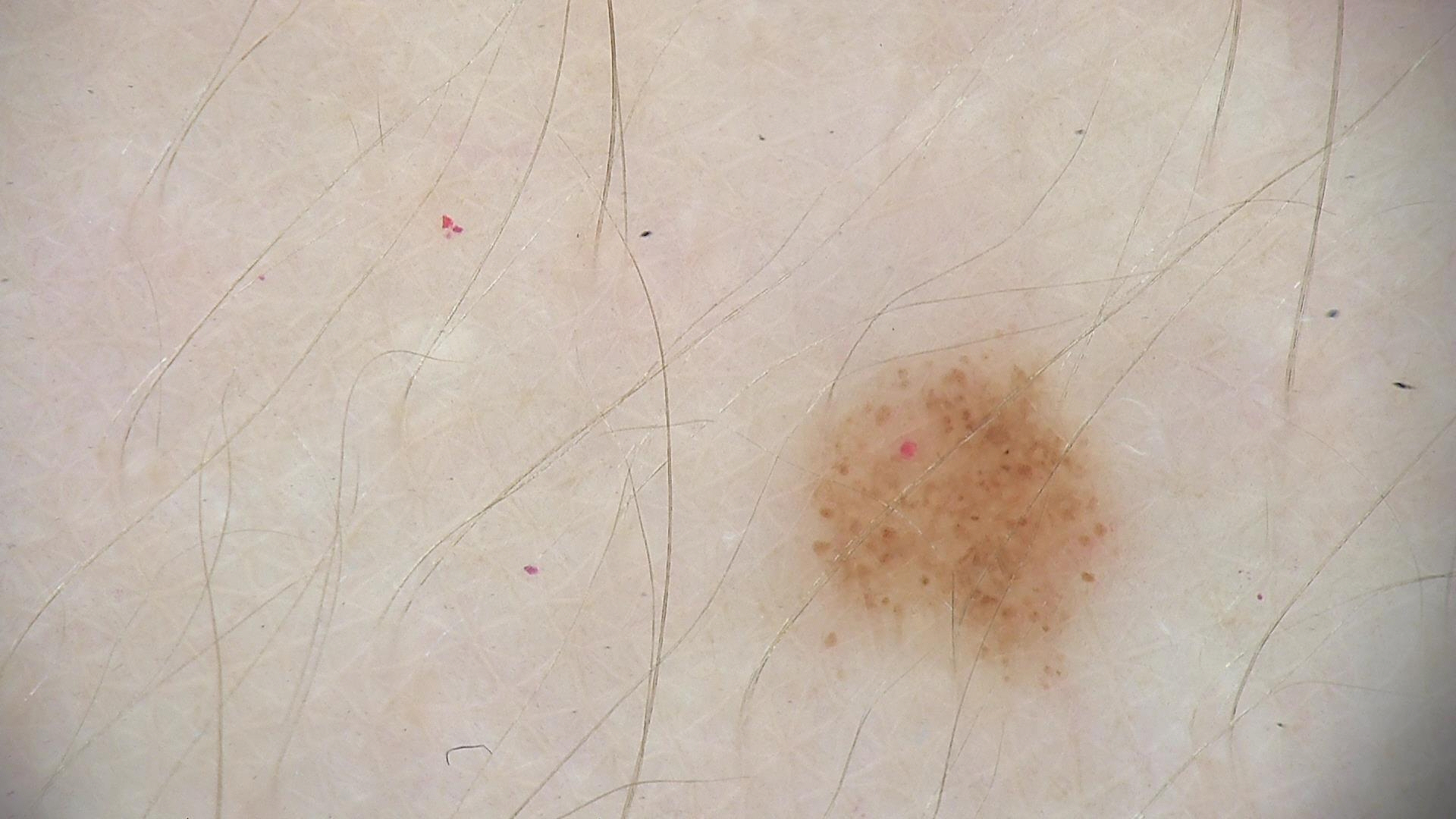• diagnostic label — dysplastic junctional nevus (expert consensus)